The patient notes pain and bothersome appearance. The leg is involved. Self-categorized by the patient as a rash. Texture is reported as fluid-filled and raised or bumpy. The photograph was taken at a distance. Reported duration is three to twelve months:
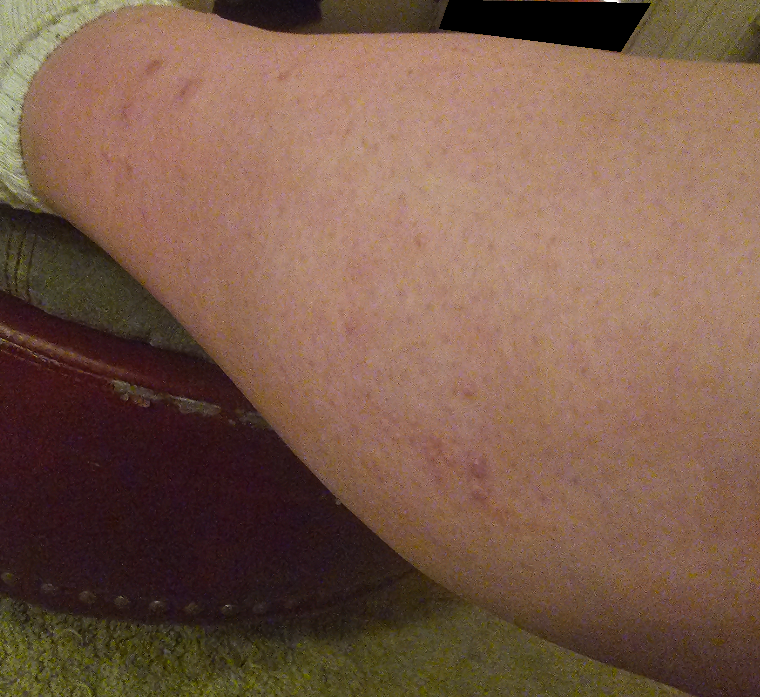  differential:
    leading:
      - Urticaria